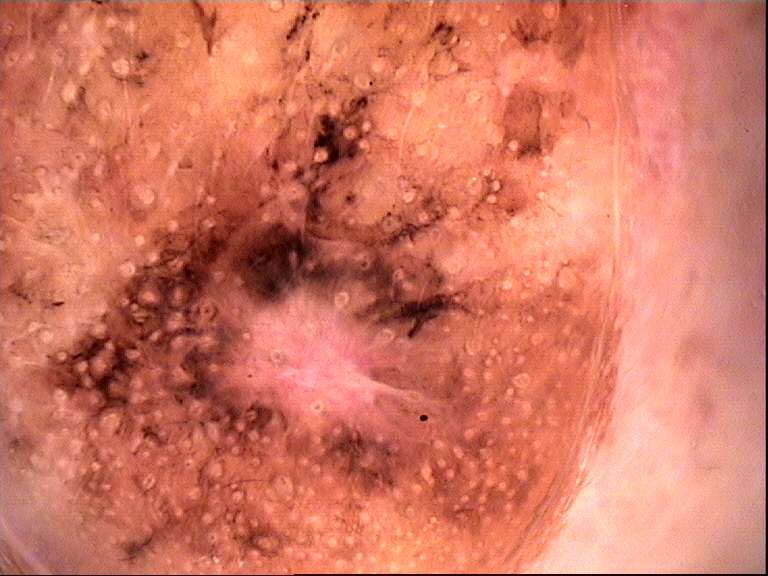Confirmed on histopathology as a malignancy — a lentigo maligna.